Reported duration is more than one year · the patient described the issue as a rash · the leg is involved · female contributor, age 50–59 · the patient notes pain · the patient notes the lesion is raised or bumpy · a close-up photograph — 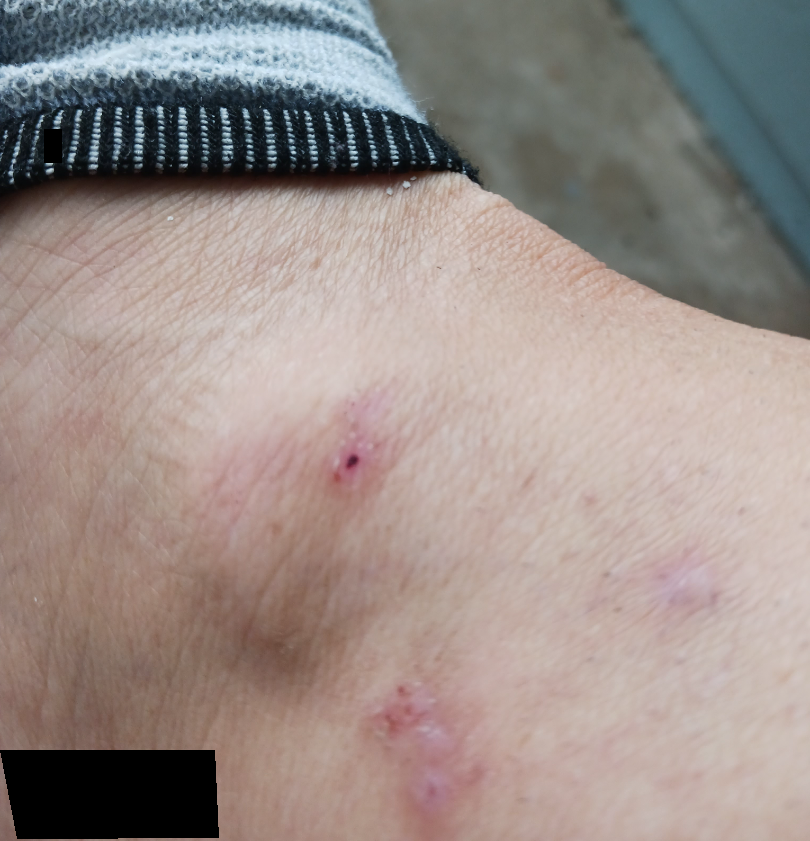differential diagnosis = most likely Insect Bite.